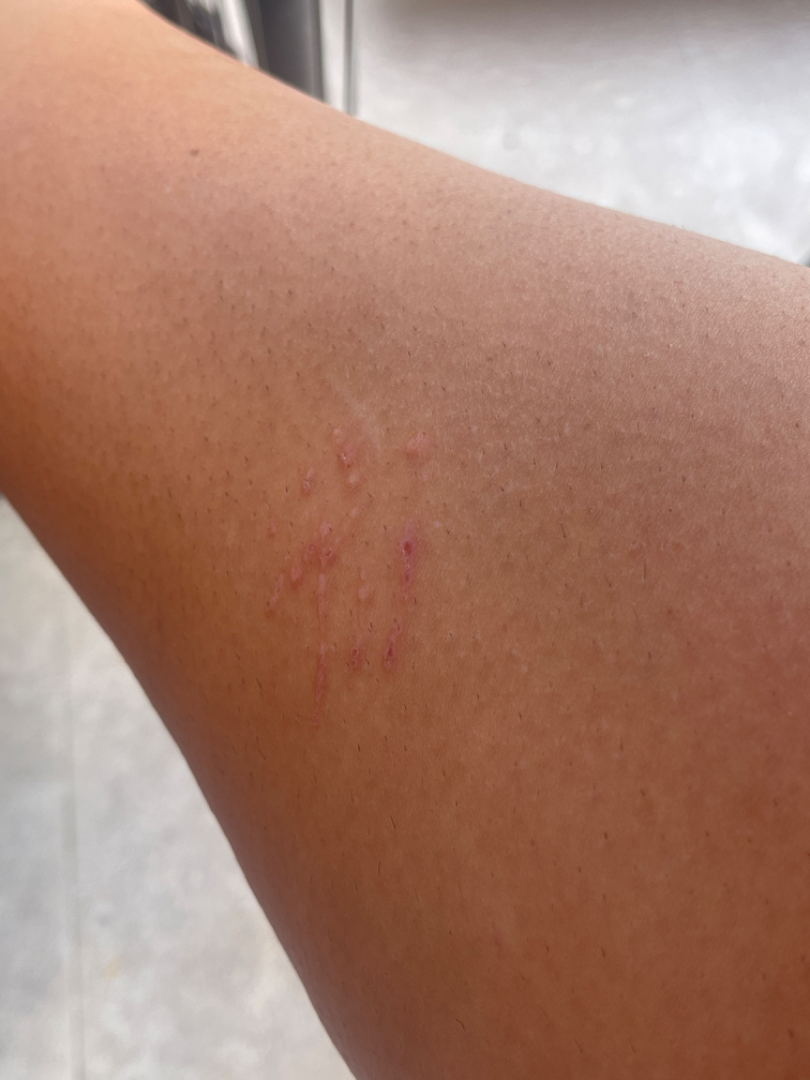Patient information: An image taken at an angle. The patient is a female aged 18–29. FST III; human graders estimated MST 5 (US pool) or 3 (India pool). The lesion is described as fluid-filled and raised or bumpy. Symptoms reported: itching, burning, bothersome appearance and enlargement. The leg is involved. The patient described the issue as a rash. No relevant systemic symptoms. The patient notes the condition has been present for one to four weeks. Review: The reviewing dermatologist's impression was: the favored diagnosis is Animal bite - wound.